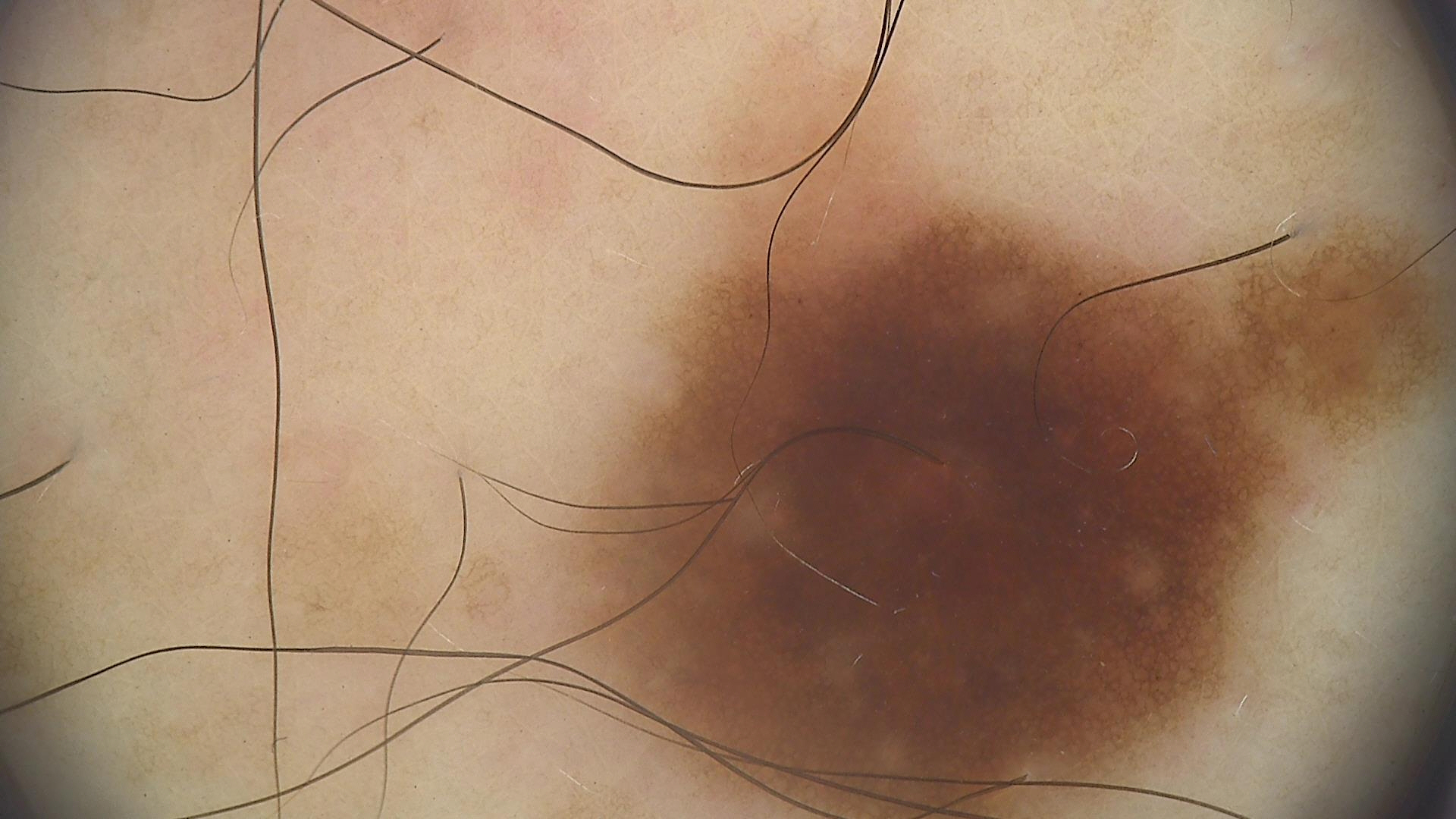Conclusion: The diagnostic label was a benign lesion — a dysplastic junctional nevus.